A clinical photo of a skin lesion taken with a smartphone; a subject in their 80s — 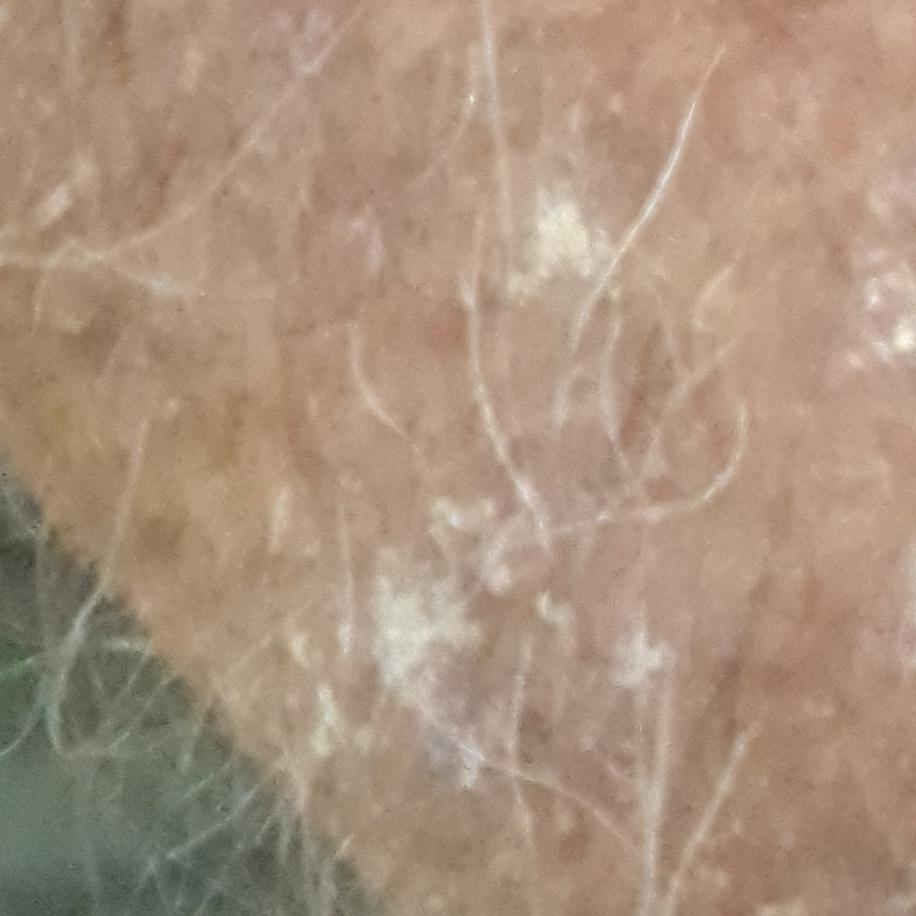{"lesion_location": "a forearm", "symptoms": {"present": ["itching"]}, "diagnosis": {"name": "actinic keratosis", "code": "ACK", "malignancy": "indeterminate", "confirmation": "clinical consensus"}}